A skin lesion imaged with a dermatoscope.
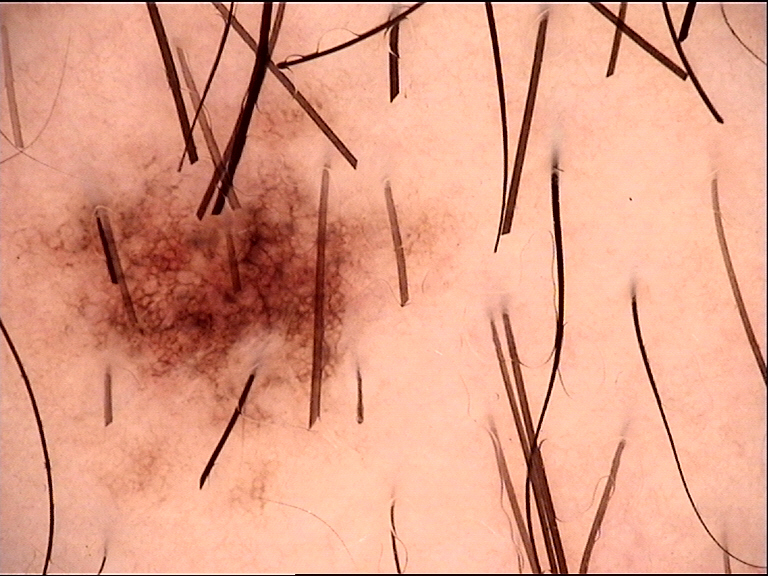The diagnostic label was a dysplastic junctional nevus.